A male subject in their mid- to late 70s; dermoscopy of a skin lesion — 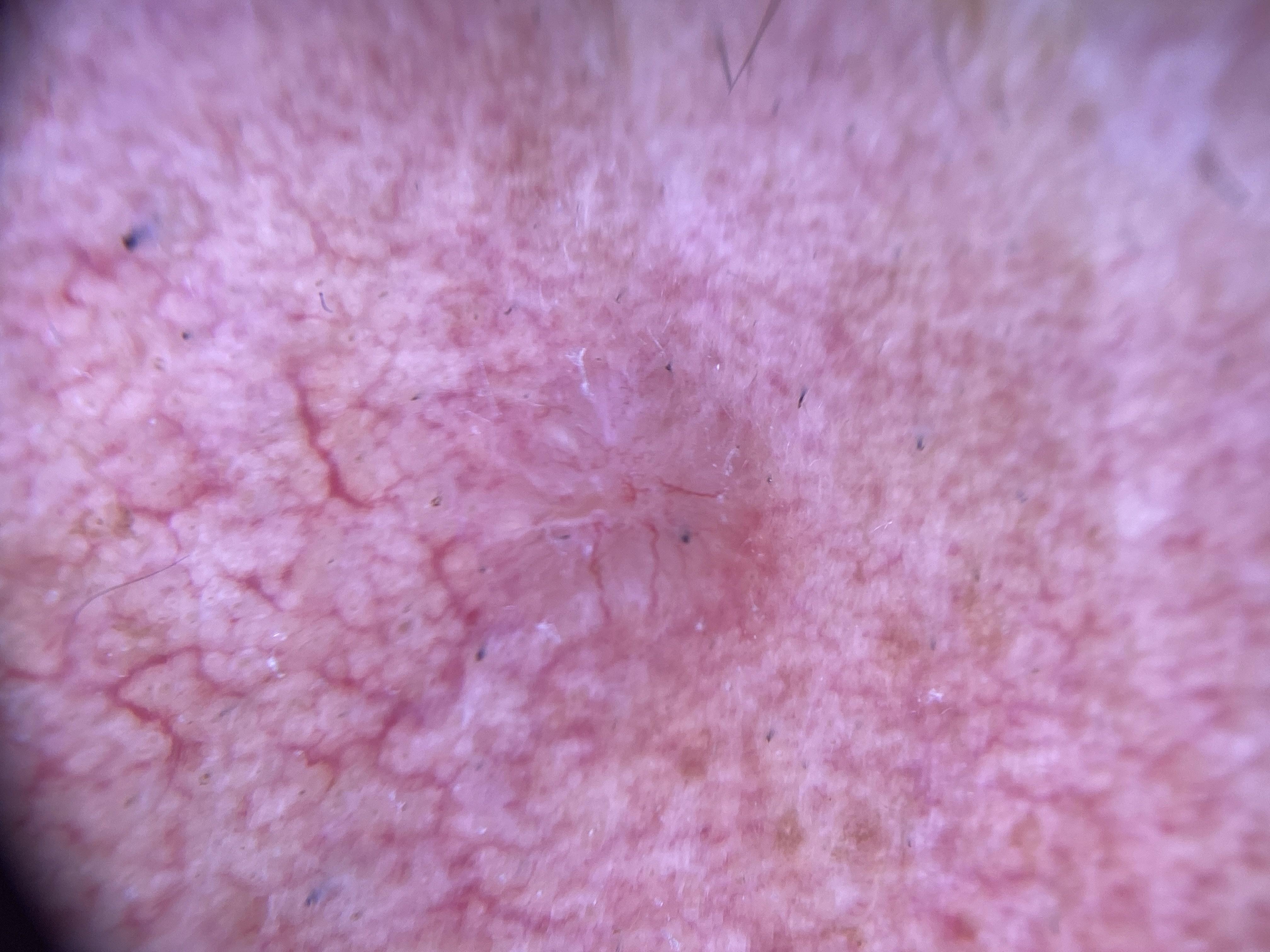body site=the head or neck | pathology=Basal cell carcinoma (biopsy-proven).